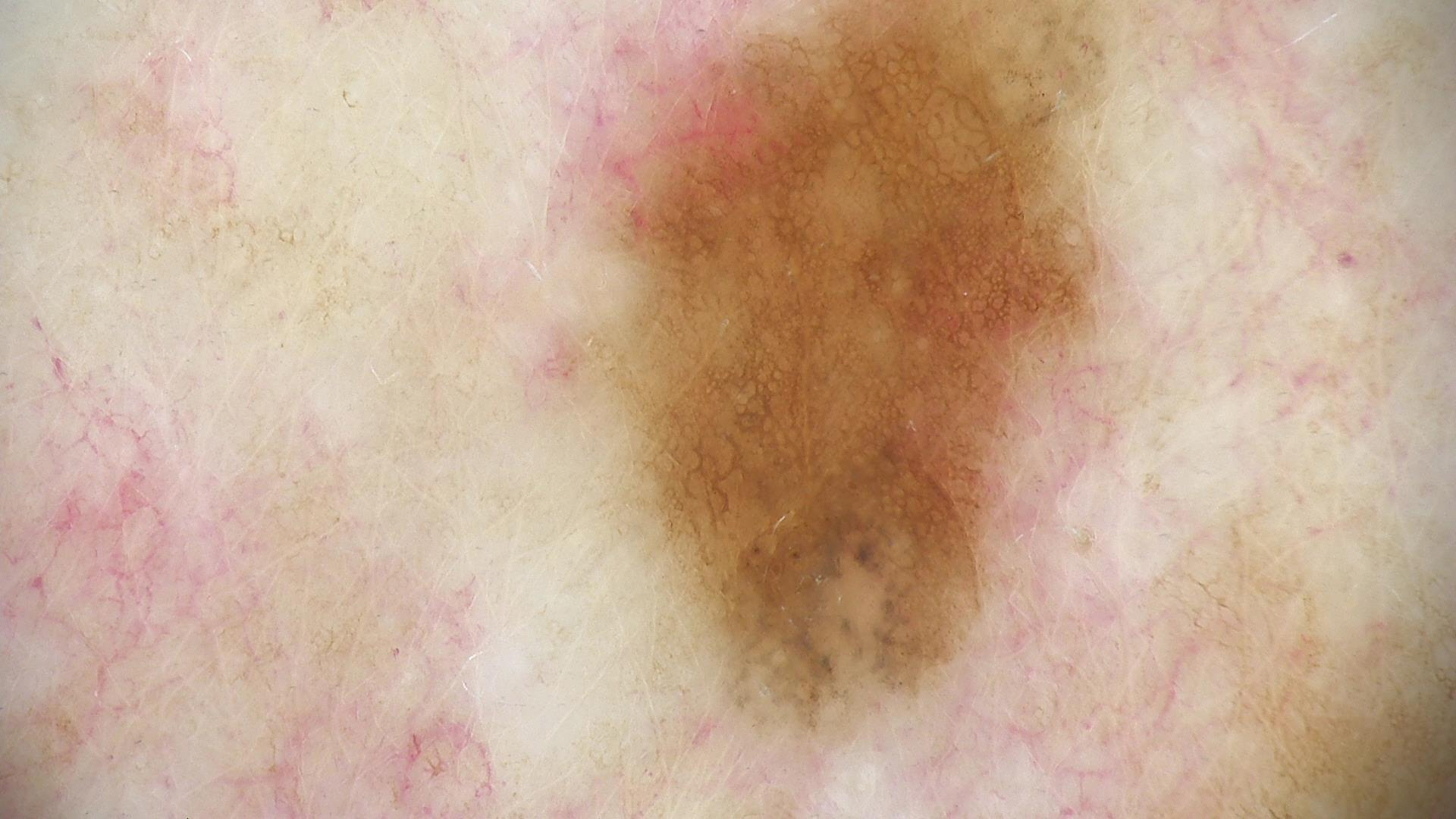The diagnosis was a benign lesion — a dysplastic junctional nevus.